A dermoscopy image of a single skin lesion.
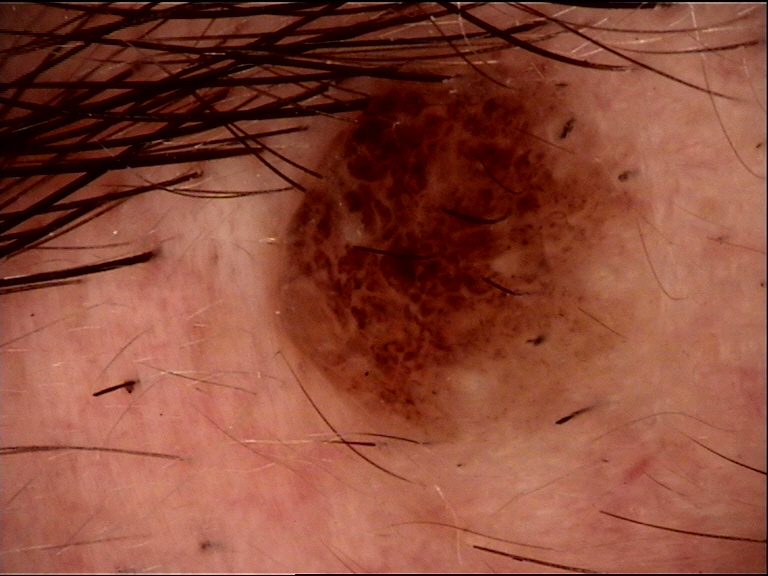subtype = banal
label = compound nevus (expert consensus)